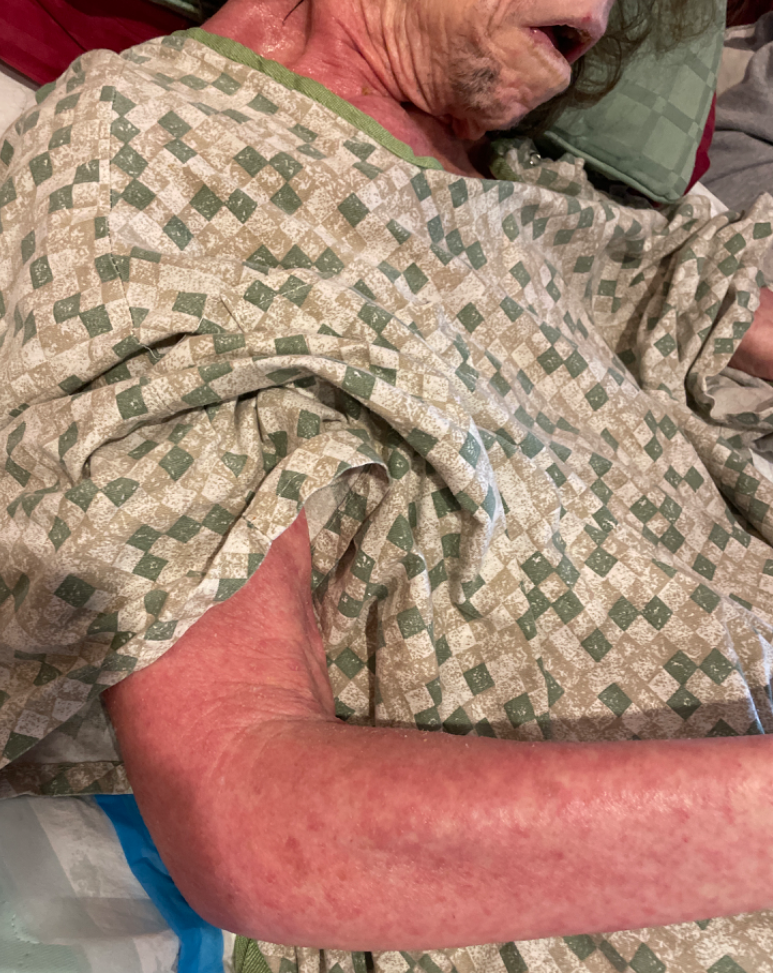The condition could not be reliably identified from the image. The patient considered this a rash. The front of the torso, head or neck, arm and leg are involved. The photograph is a close-up of the affected area. The contributor is a female aged 60–69. The lesion is described as rough or flaky. Reported duration is one to four weeks. The patient reported no systemic symptoms.